A female subject 84 years old. A clinical photograph of a skin lesion — 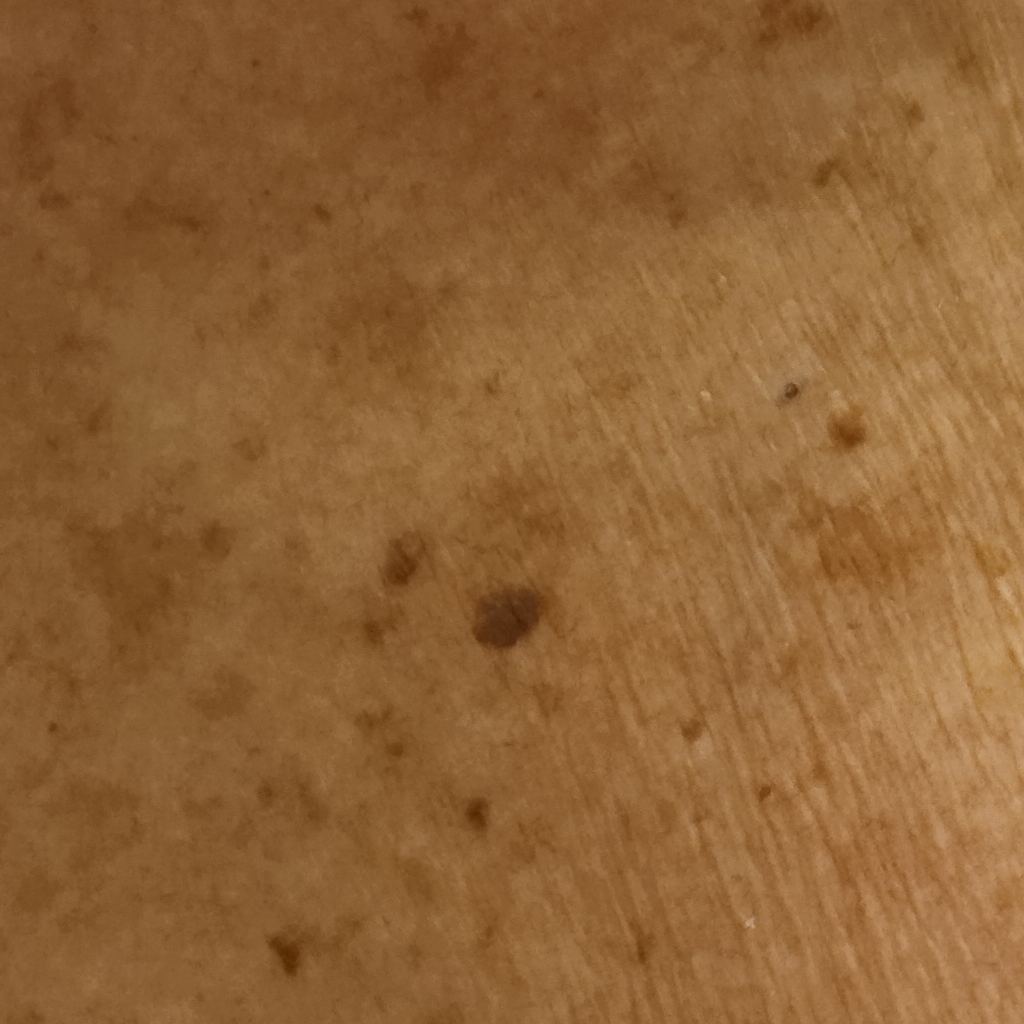The lesion is on the torso. The dermatologists' assessment was a seborrheic keratosis.